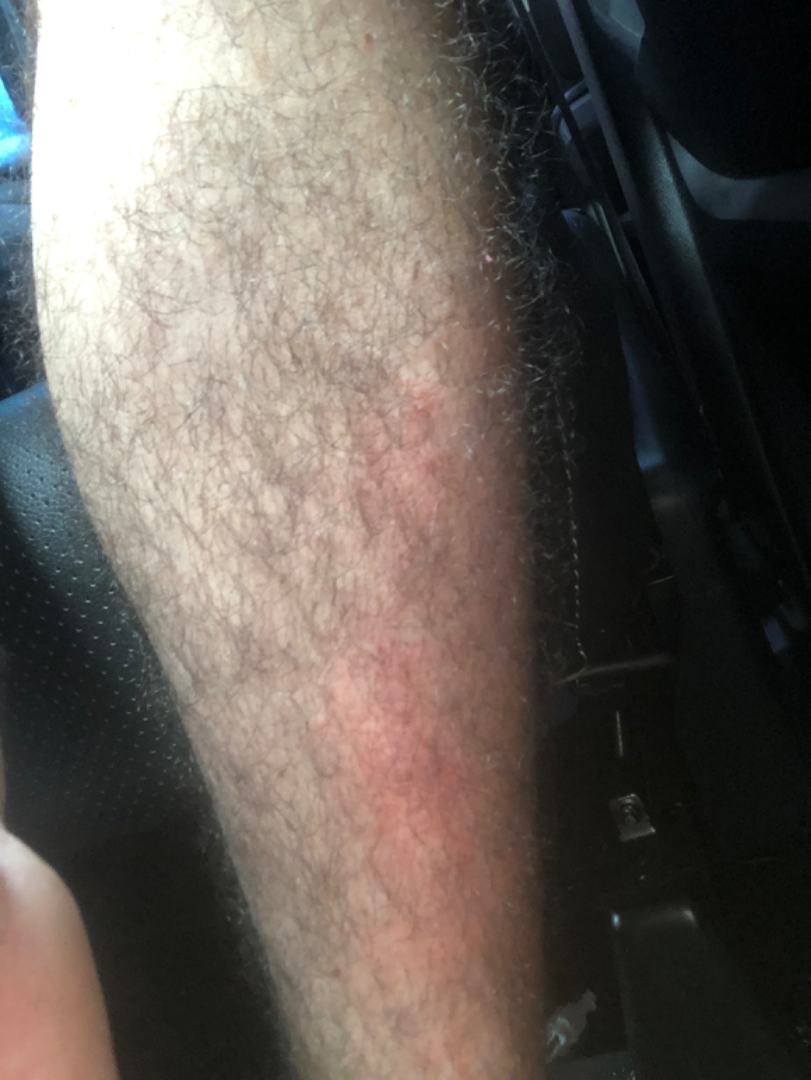Texture is reported as raised or bumpy and flat. The lesion is associated with itching and bothersome appearance. The patient described the issue as a rash. The lesion involves the leg. The photograph is a close-up of the affected area. Present for less than one week. The patient is a male aged 18–29. The reviewing clinician's impression was: the differential, in no particular order, includes Impetigo, Cellulitis and Eczema.